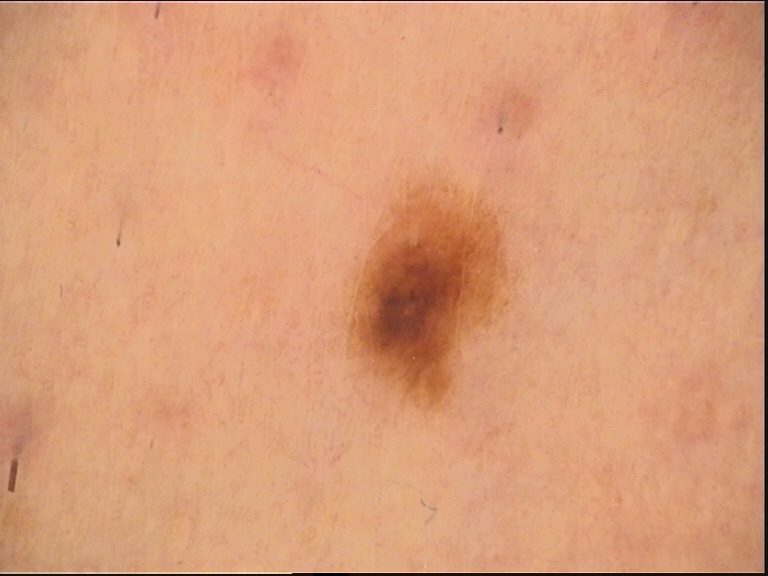{
  "image": "dermatoscopy",
  "diagnosis": {
    "name": "dysplastic junctional nevus",
    "code": "jd",
    "malignancy": "benign",
    "super_class": "melanocytic",
    "confirmation": "expert consensus"
  }
}